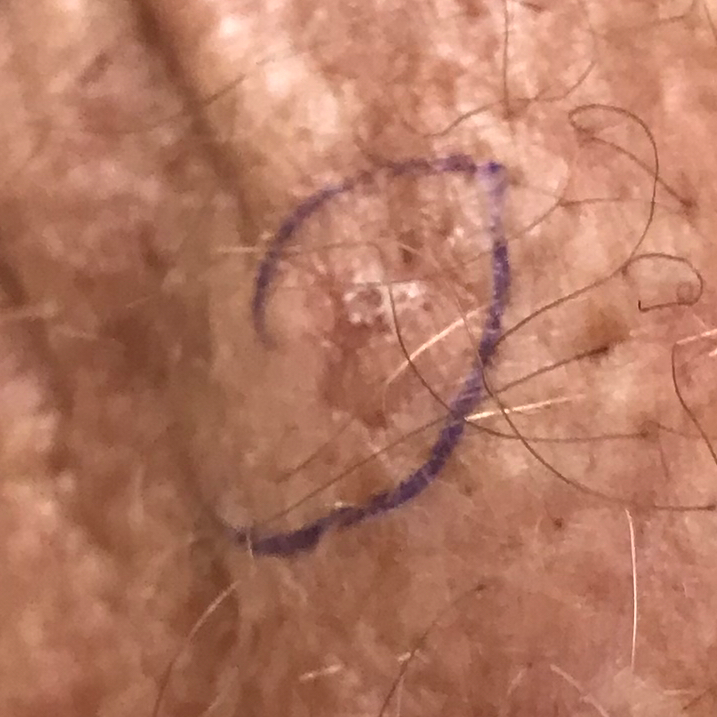Findings:
A clinical photo of a skin lesion taken with a smartphone. A subject in their early 60s. The lesion is on an arm. No symptoms reported.
Conclusion:
The diagnostic impression was an actinic keratosis.